A dermatoscopic image of a skin lesion:
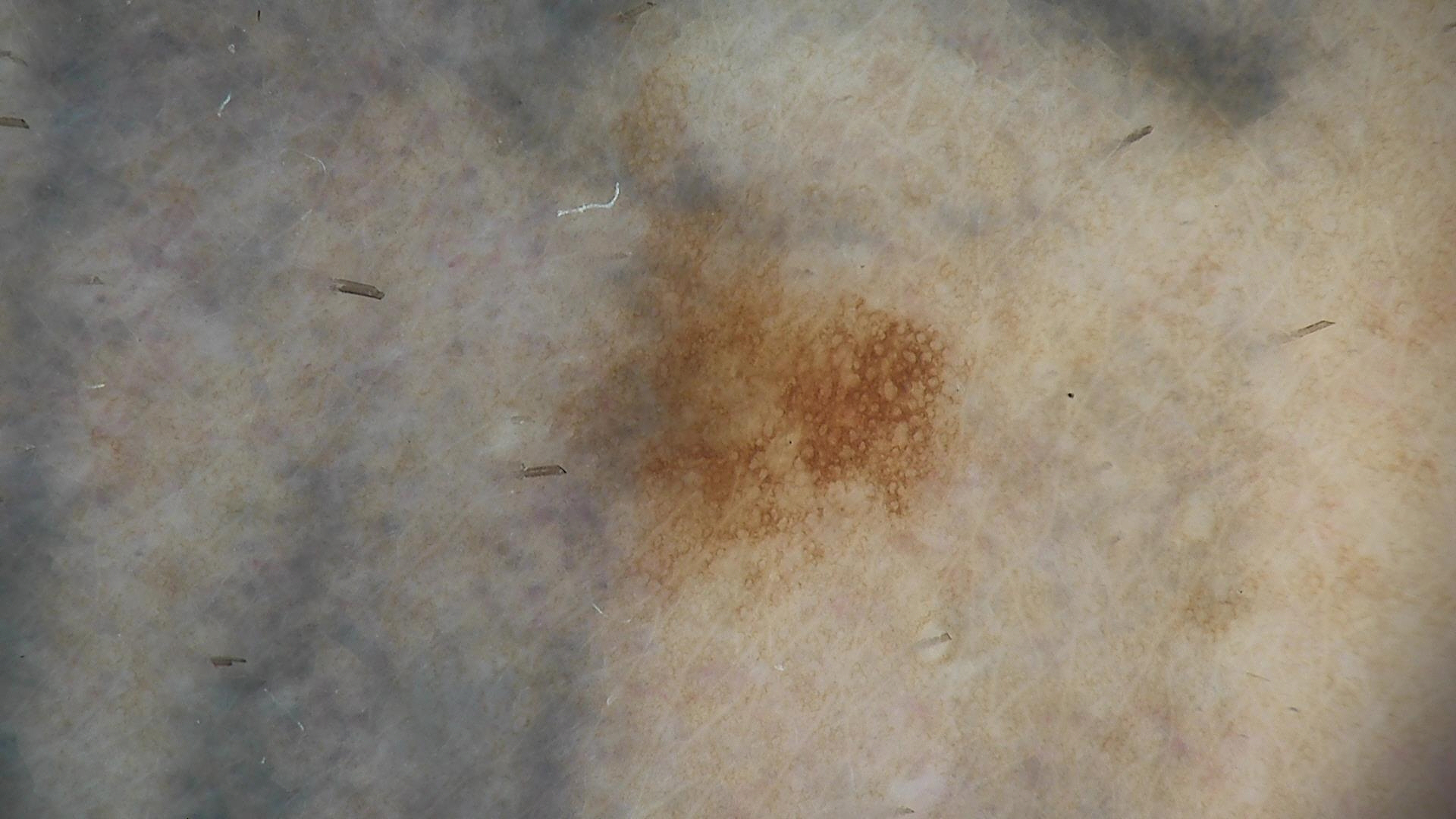Diagnosed as a benign lesion — a dysplastic junctional nevus.